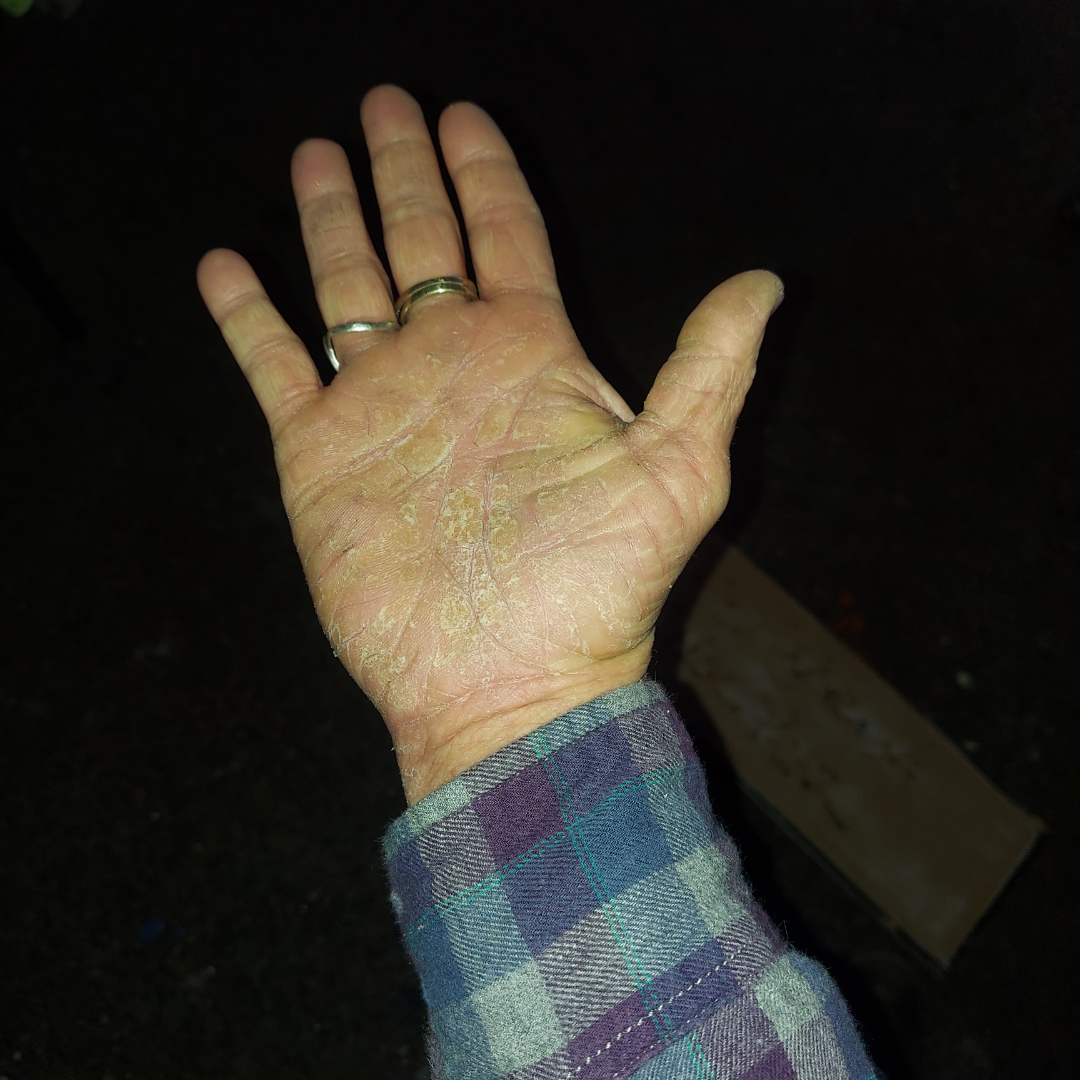Patient information:
The patient notes bothersome appearance, itching, pain and bleeding. The photo was captured at a distance. Female contributor, age 40–49. Present for more than one year. Texture is reported as rough or flaky. The patient considered this a rash. No associated systemic symptoms reported. Located on the palm.
Review:
The reviewing clinician's impression was: the favored diagnosis is Eczema; also raised was Hyperkeratosis; less likely is Keratoderma.